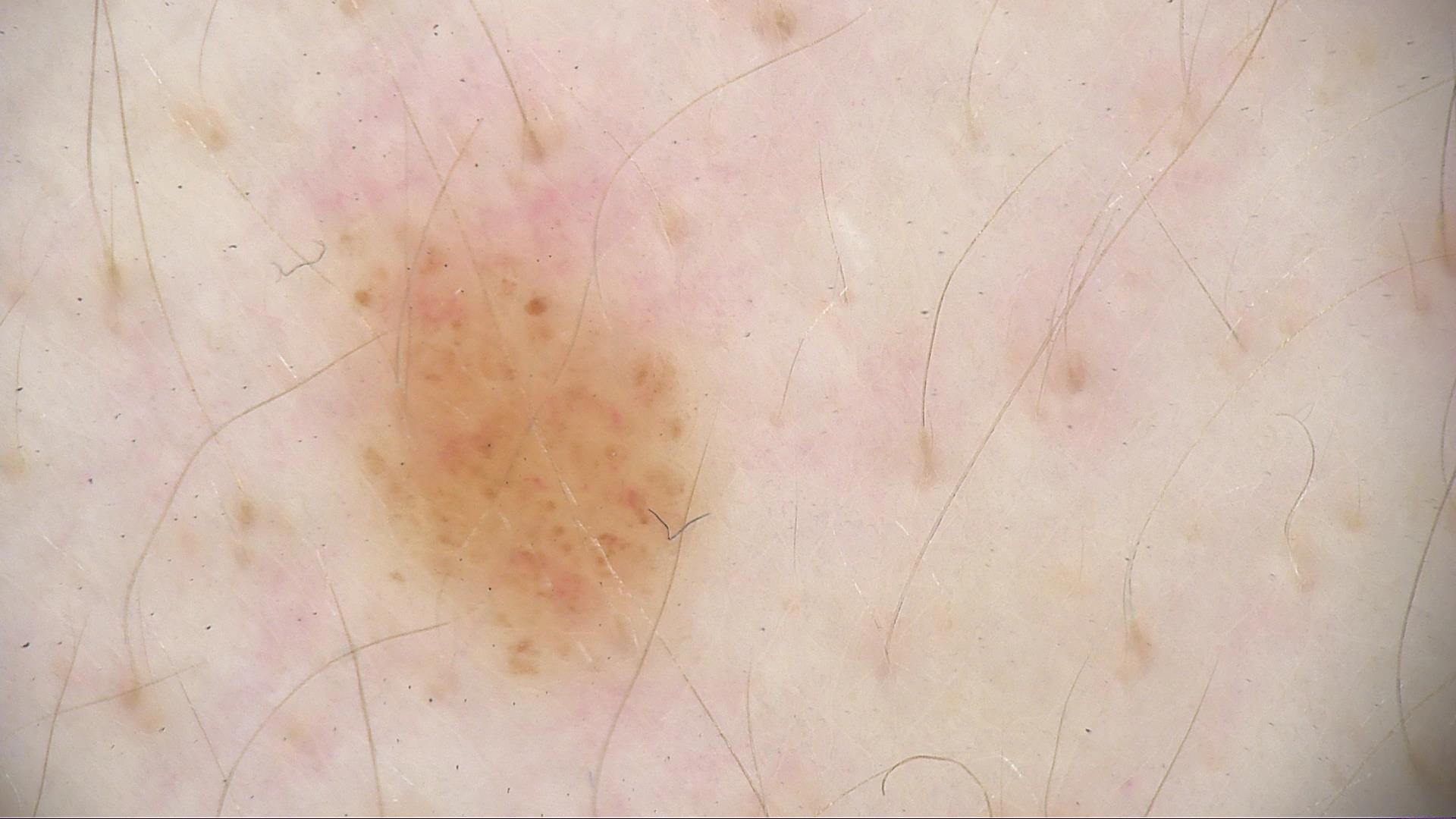| feature | finding |
|---|---|
| imaging | dermoscopy |
| lesion type | banal |
| class | dermal nevus (expert consensus) |